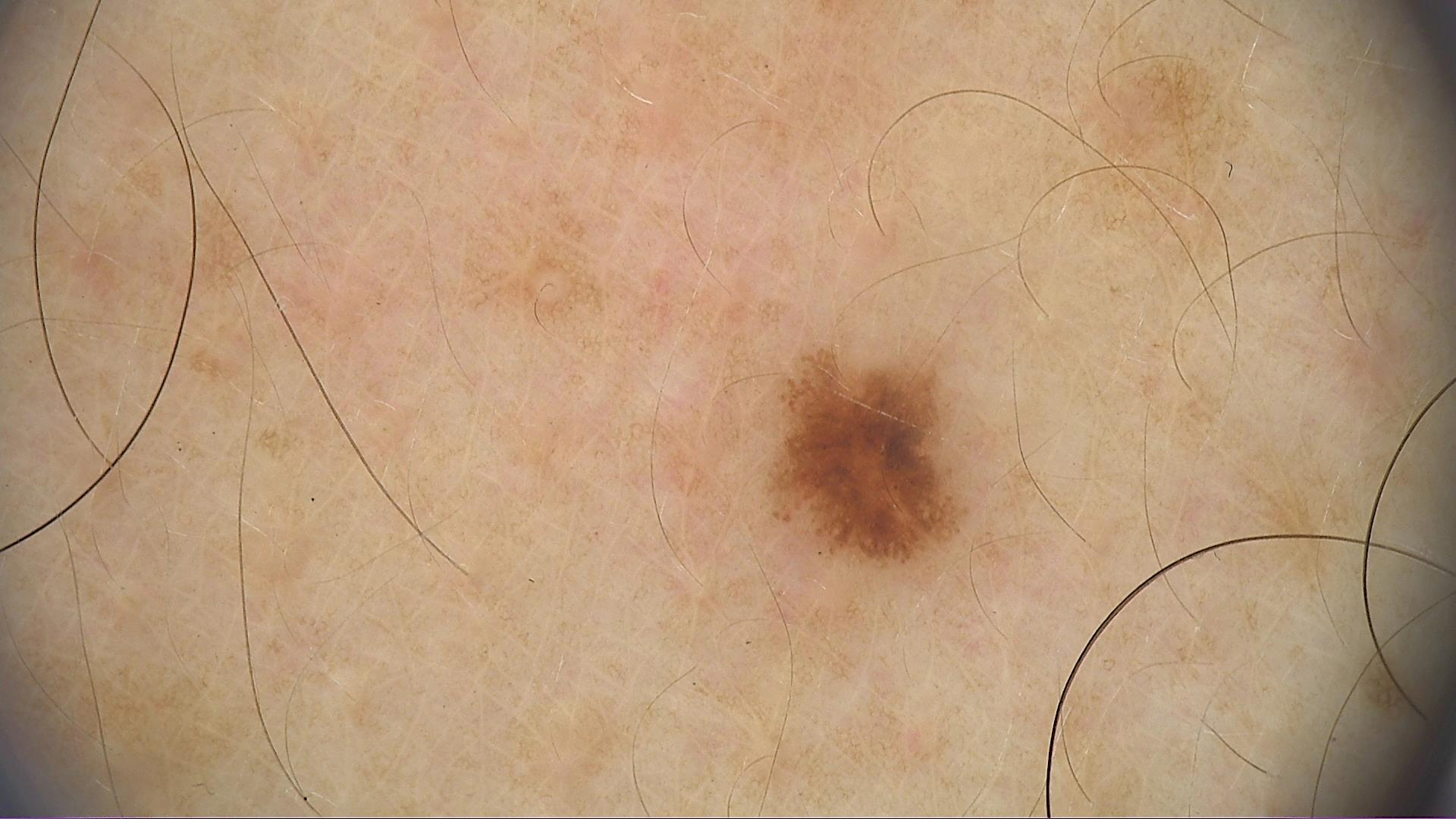image — dermoscopy | class — dysplastic junctional nevus (expert consensus).